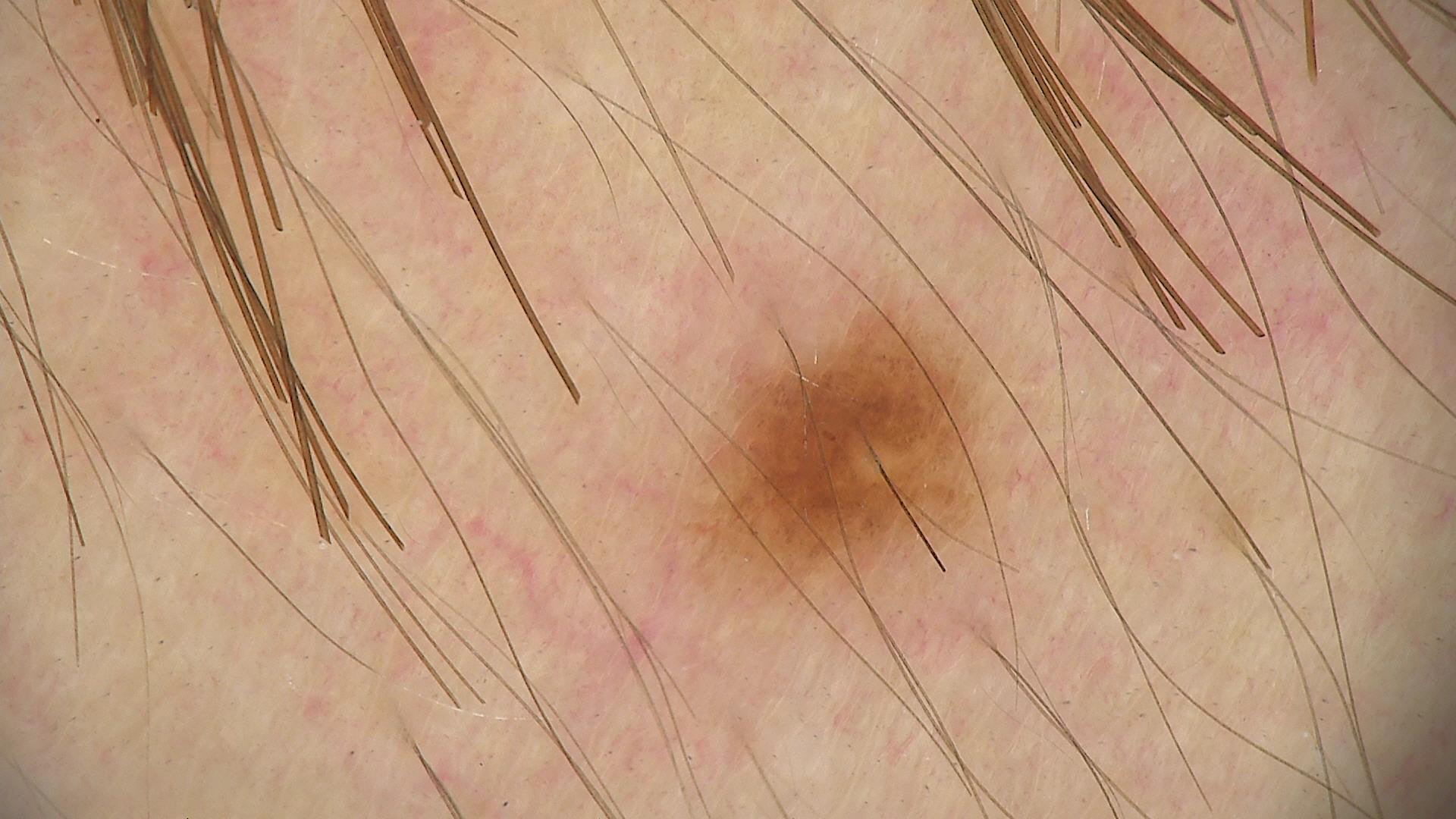Conclusion: The diagnostic label was a dysplastic junctional nevus.